A patient 58 years of age · a clinical photograph of a skin lesion.
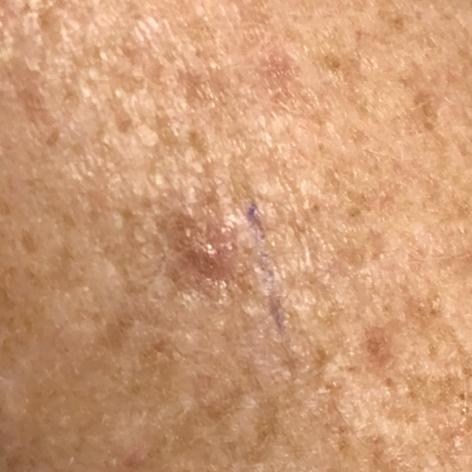Q: What is the anatomic site?
A: a forearm
Q: What was the clinical impression?
A: actinic keratosis (clinical consensus)